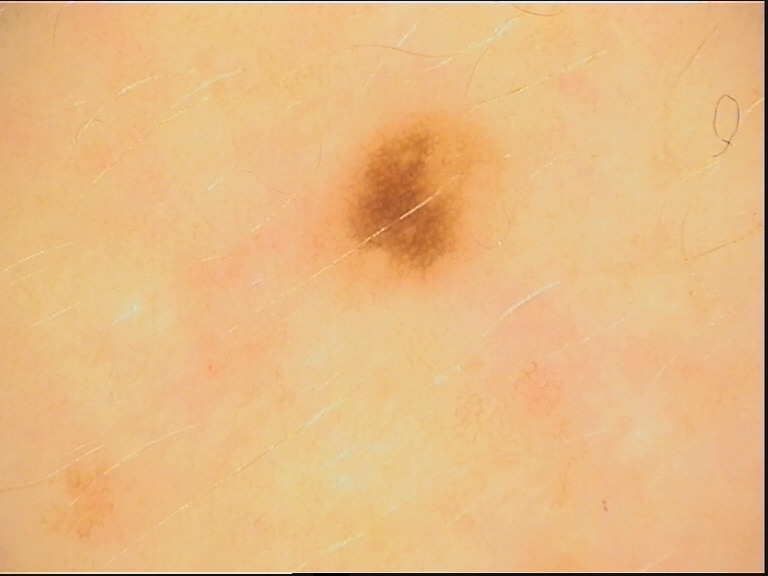{
  "diagnosis": {
    "name": "junctional nevus",
    "code": "jb",
    "malignancy": "benign",
    "super_class": "melanocytic",
    "confirmation": "expert consensus"
  }
}